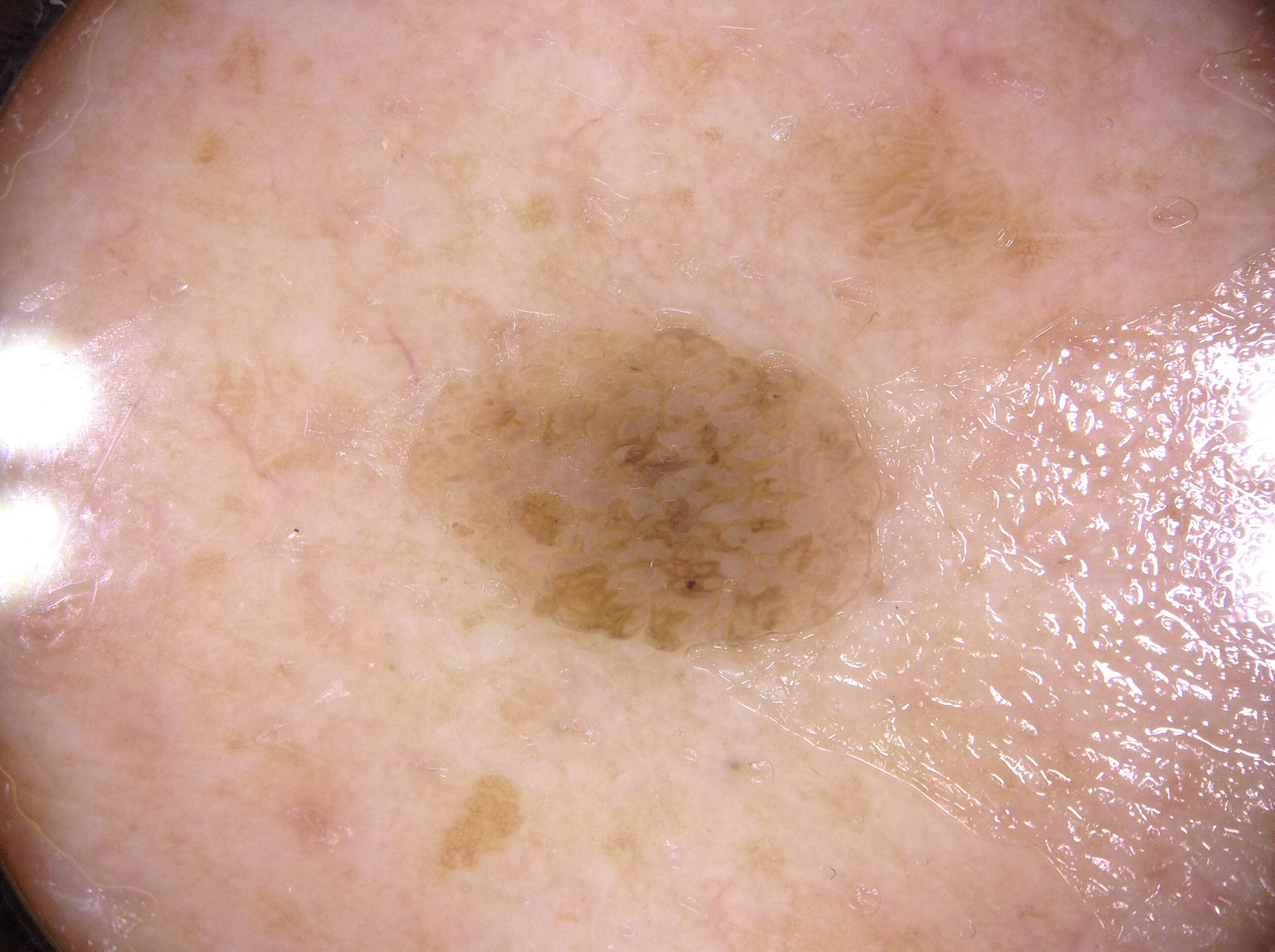Notes:
* modality — dermoscopy
* patient — male, aged 58-62
* size — moderate
* bounding box — (405, 307, 897, 666)
* features — pigment network; absent: negative network, streaks, and milia-like cysts
* assessment — a seborrheic keratosis, a lesion of keratinocytic origin